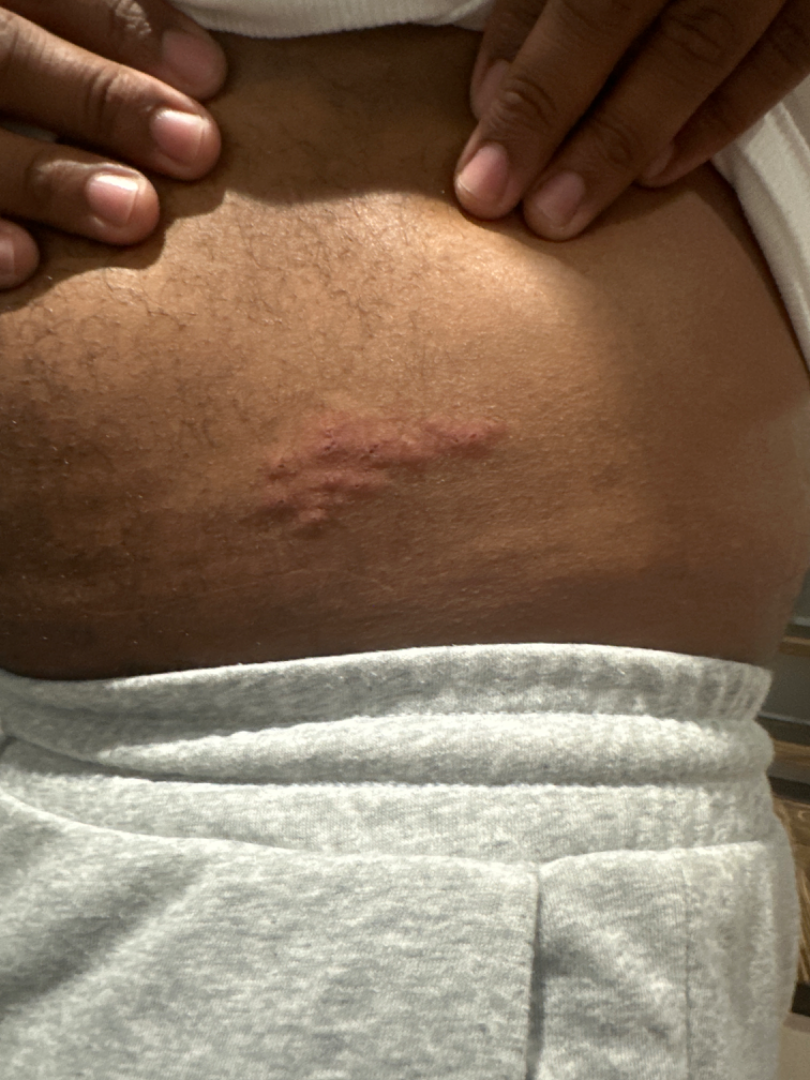diagnostic considerations=Herpes Zoster (most likely).